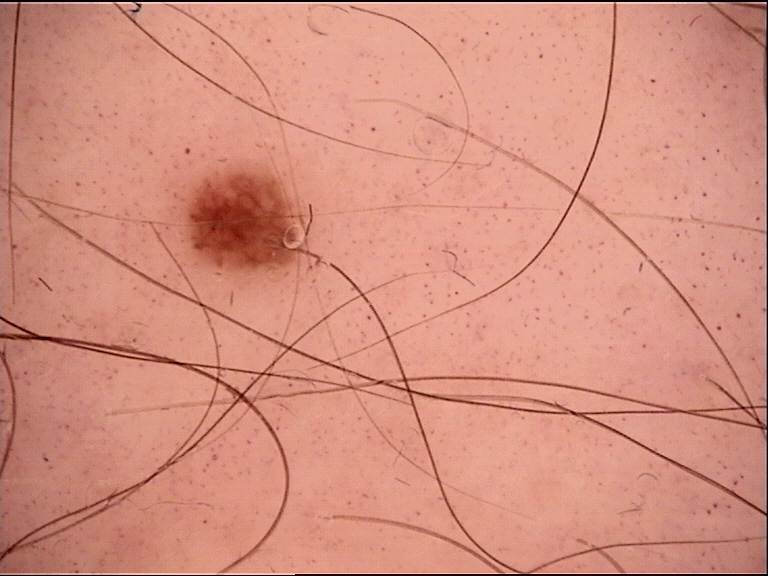Findings:
Dermoscopy of a skin lesion.
Conclusion:
The diagnosis was a benign lesion — a dysplastic junctional nevus.